A patient in their mid-50s:
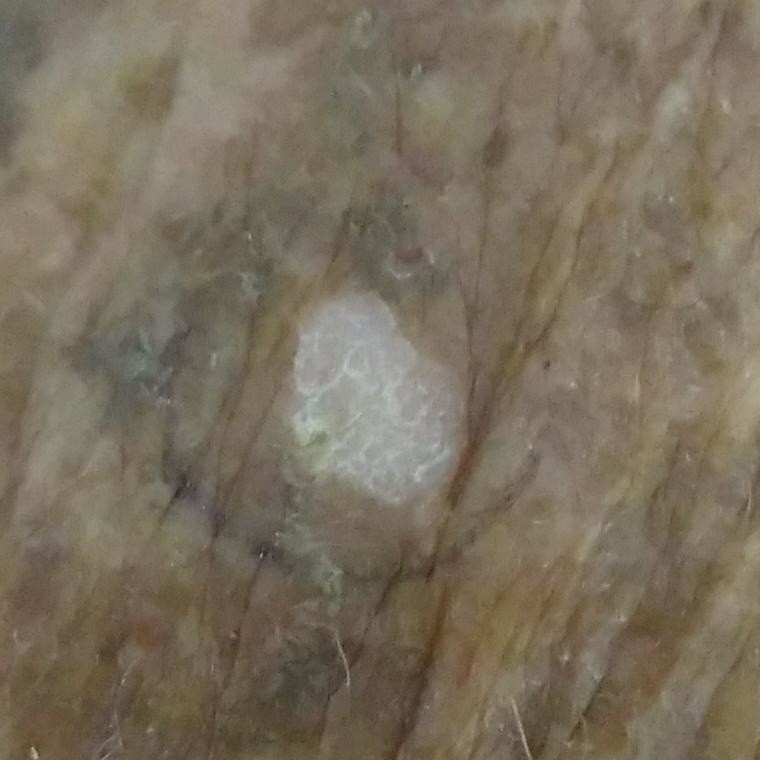– anatomic site — the face
– reported symptoms — itching
– impression — actinic keratosis (clinical consensus)